This is a dermoscopic photograph of a skin lesion — 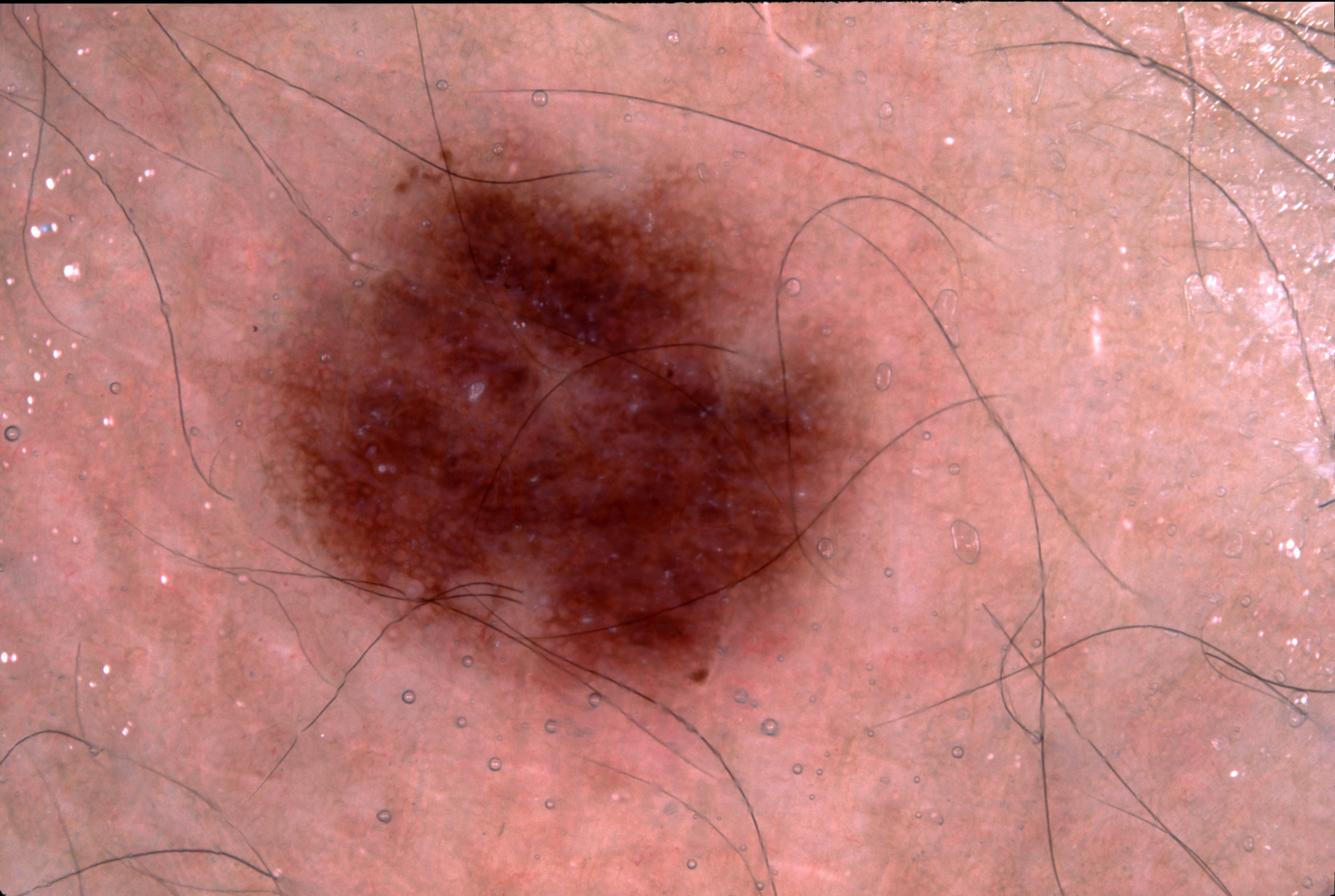Dermoscopic review identifies pigment network, with no negative network, streaks, or milia-like cysts. The lesion is located at [245, 127, 881, 706]. The diagnostic assessment was a melanocytic nevus, a benign skin lesion.